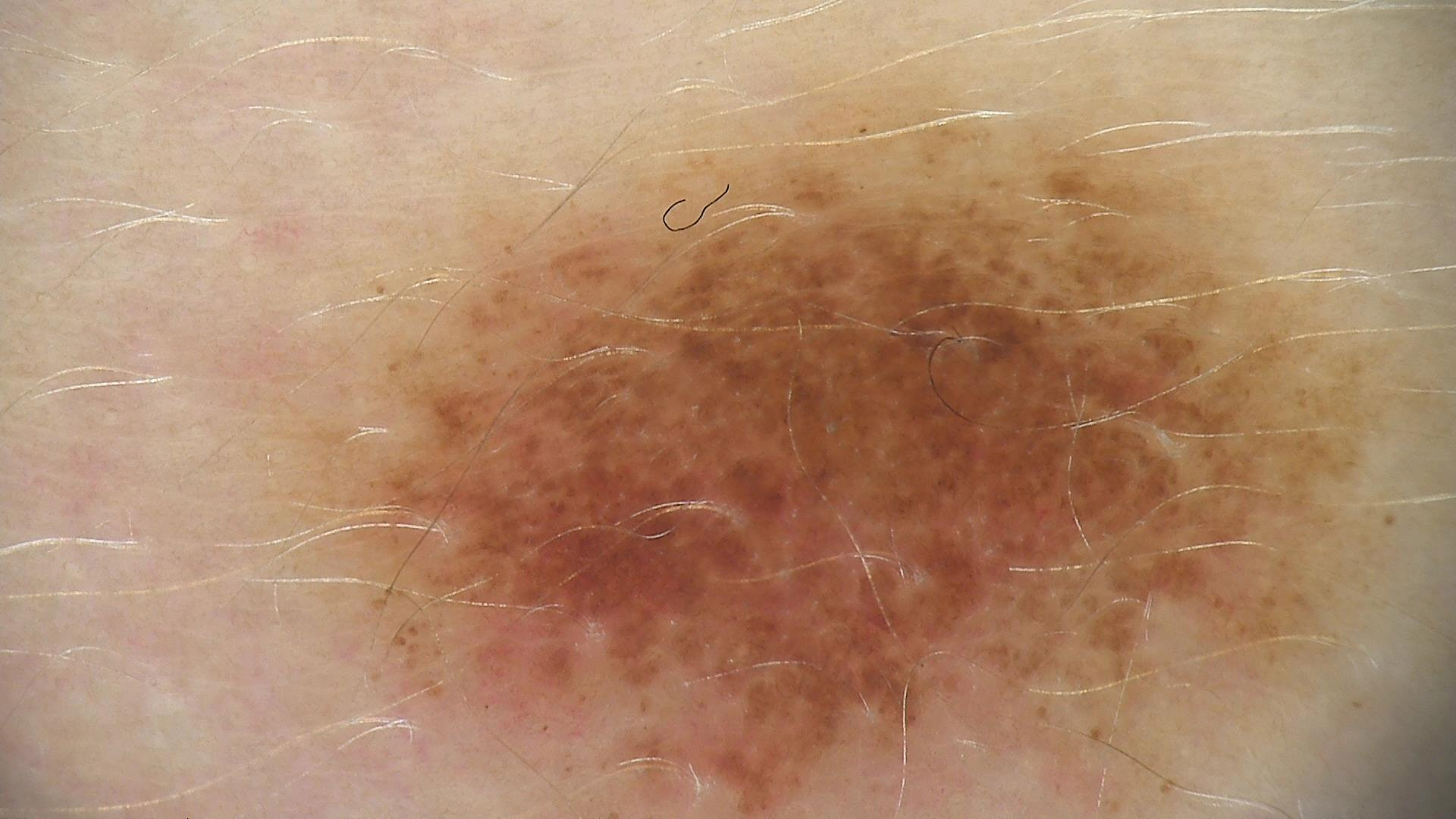Findings:
A dermoscopic photograph of a skin lesion.
Impression:
The diagnostic label was a dysplastic junctional nevus.